Female subject, age 30–39; this is a close-up image; the leg and arm are involved — 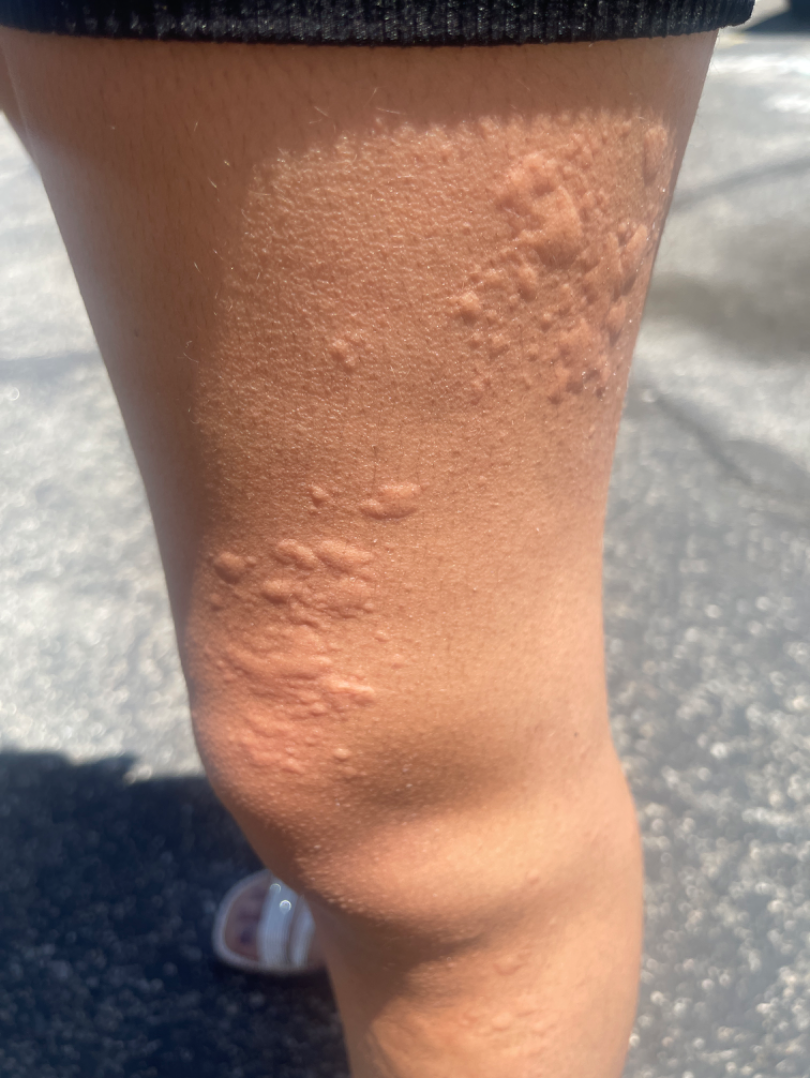Present for about one day. The patient described the issue as a rash. The contributor notes the lesion is raised or bumpy. Skin tone: Fitzpatrick phototype III. Reported lesion symptoms include bothersome appearance, itching and enlargement. On dermatologist assessment of the image, the impression is Urticaria.